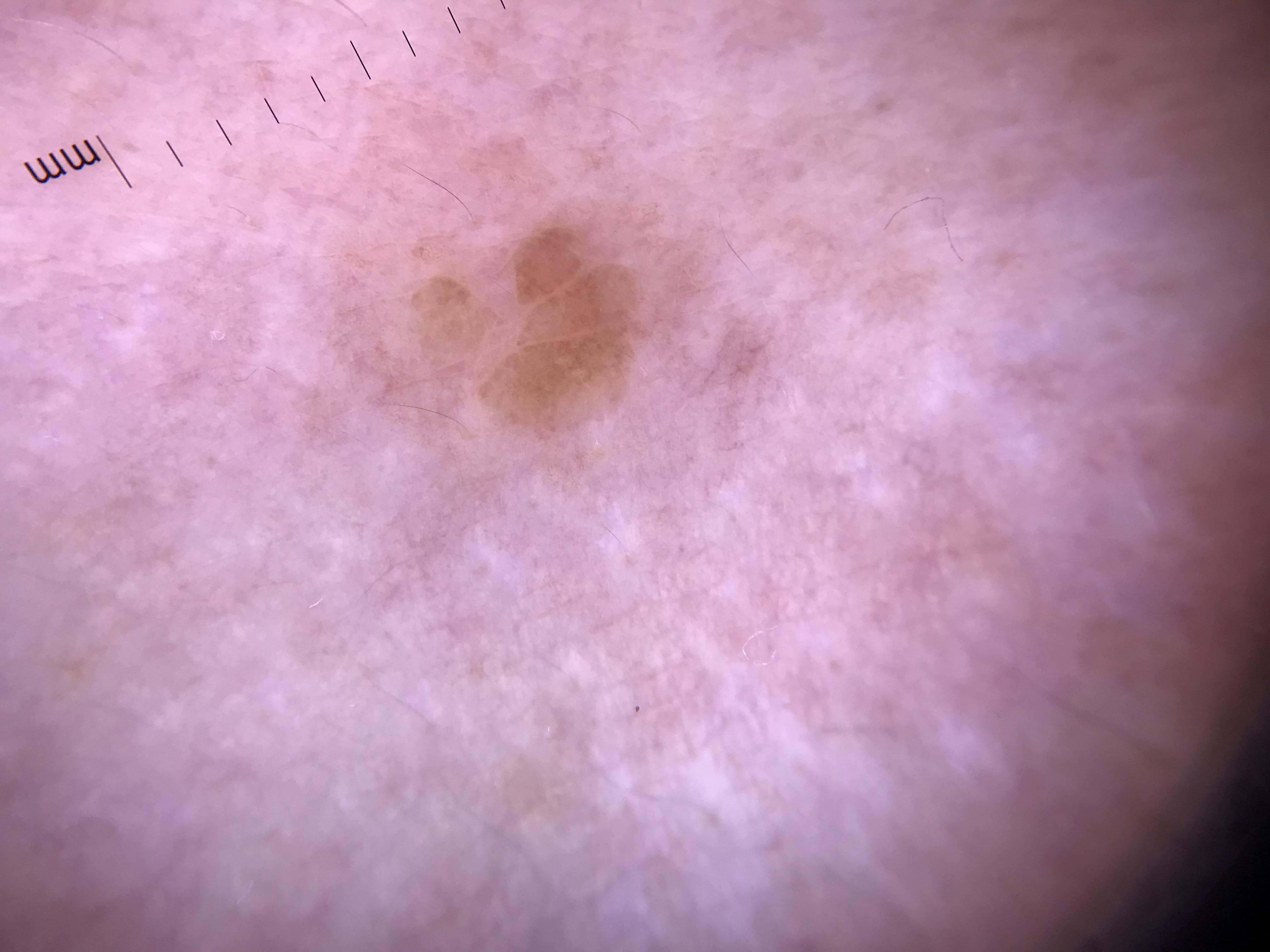A skin lesion imaged with a dermatoscope. This is a keratinocytic lesion. The diagnostic label was a benign lesion — a seborrheic keratosis.